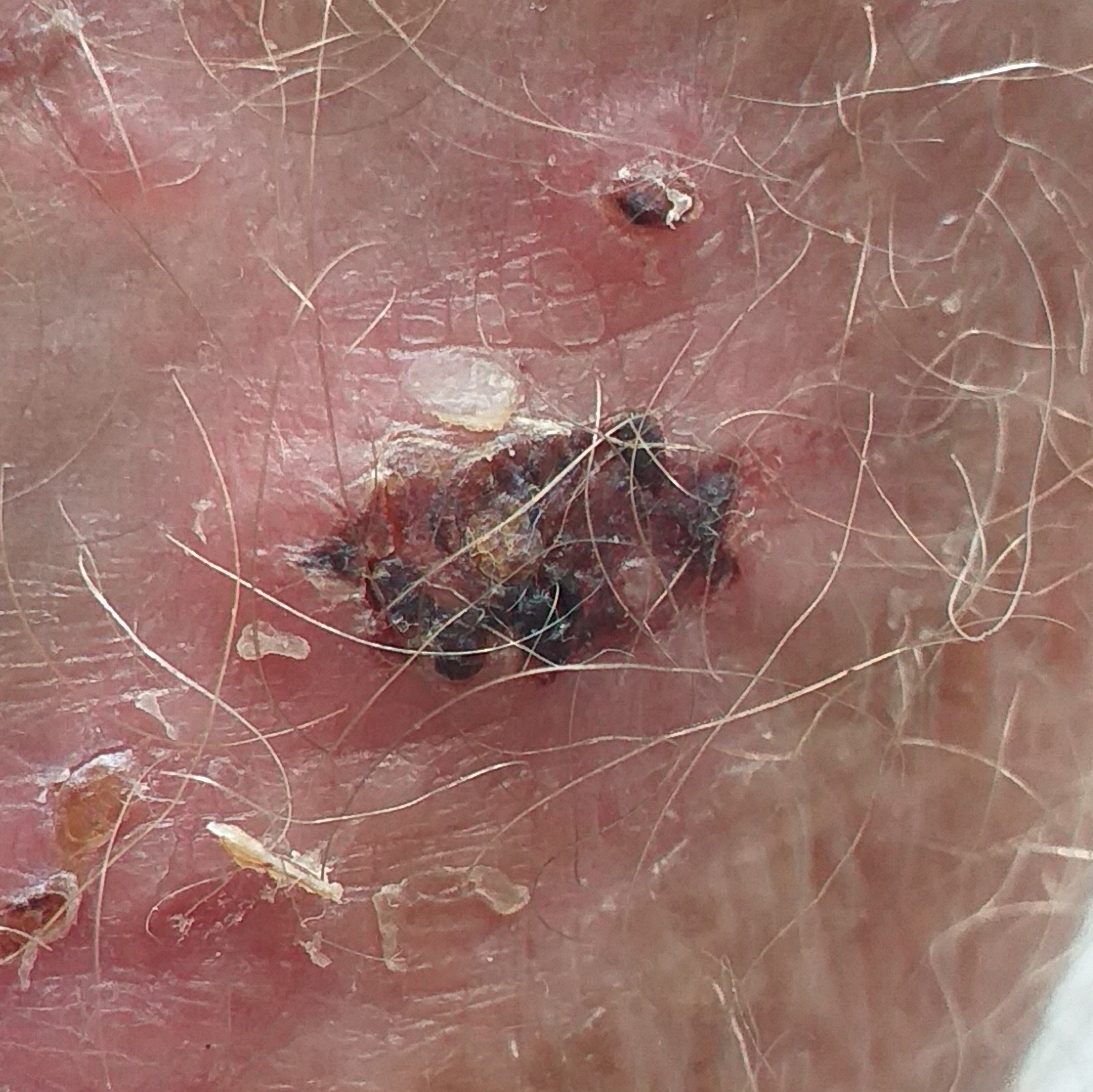Q: Skin phototype?
A: II
Q: What kind of image is this?
A: clinical photo
Q: What is the anatomic site?
A: a forearm
Q: How large is the lesion?
A: 15 × 10 mm
Q: What symptoms does the patient report?
A: bleeding, change in appearance, growth, itching
Q: What did the workup show?
A: basal cell carcinoma (biopsy-proven)